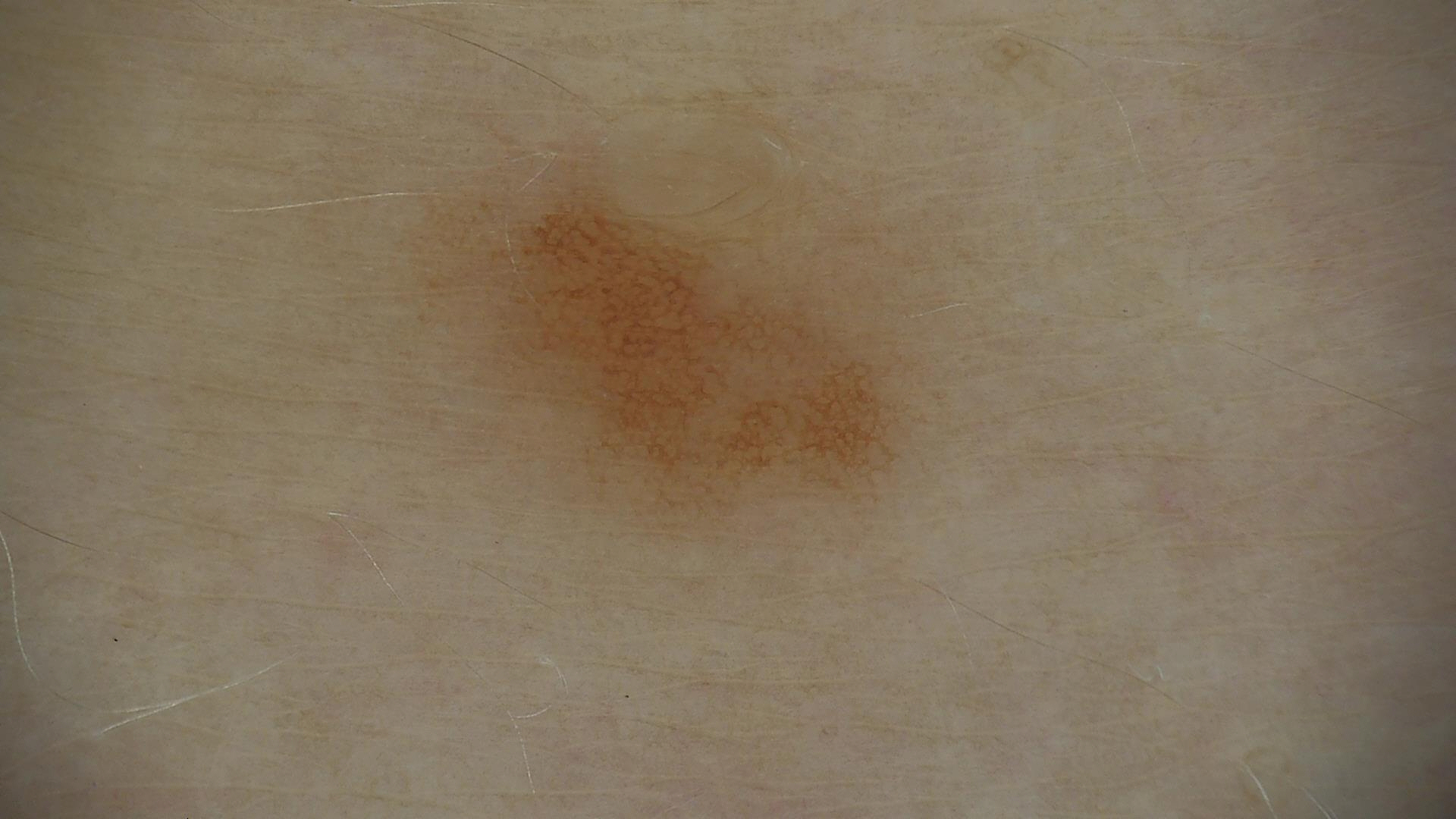label: dysplastic junctional nevus (expert consensus)